A dermoscopy image of a single skin lesion — 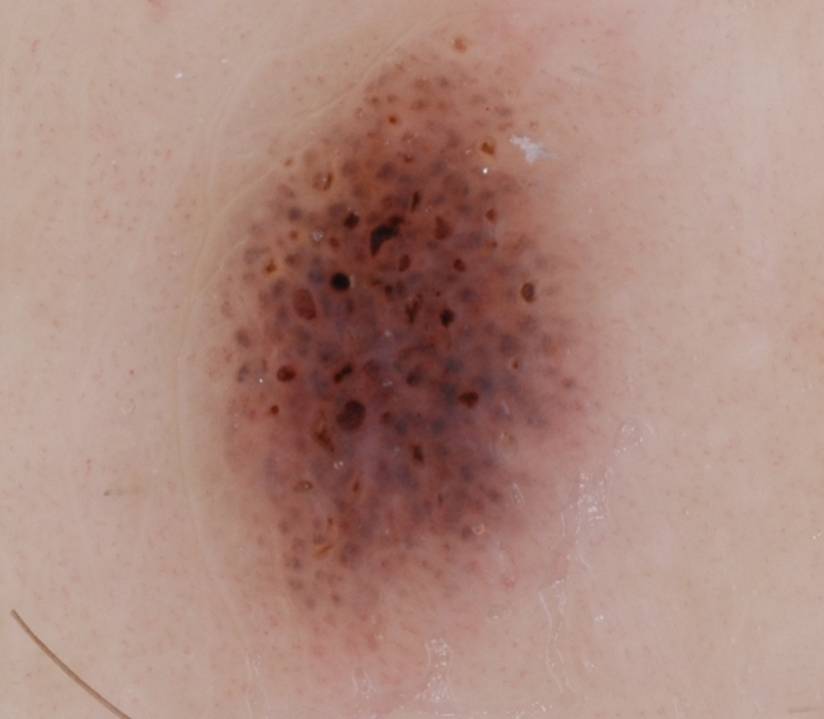{"dermoscopic_features": {"present": ["globules"], "absent": ["negative network", "streaks", "milia-like cysts", "pigment network"]}, "lesion_extent": {"approx_field_fraction_pct": 39}, "lesion_location": {"bbox_xyxy": [174, 12, 619, 694]}, "diagnosis": {"name": "melanocytic nevus", "malignancy": "benign", "lineage": "melanocytic", "provenance": "clinical"}}